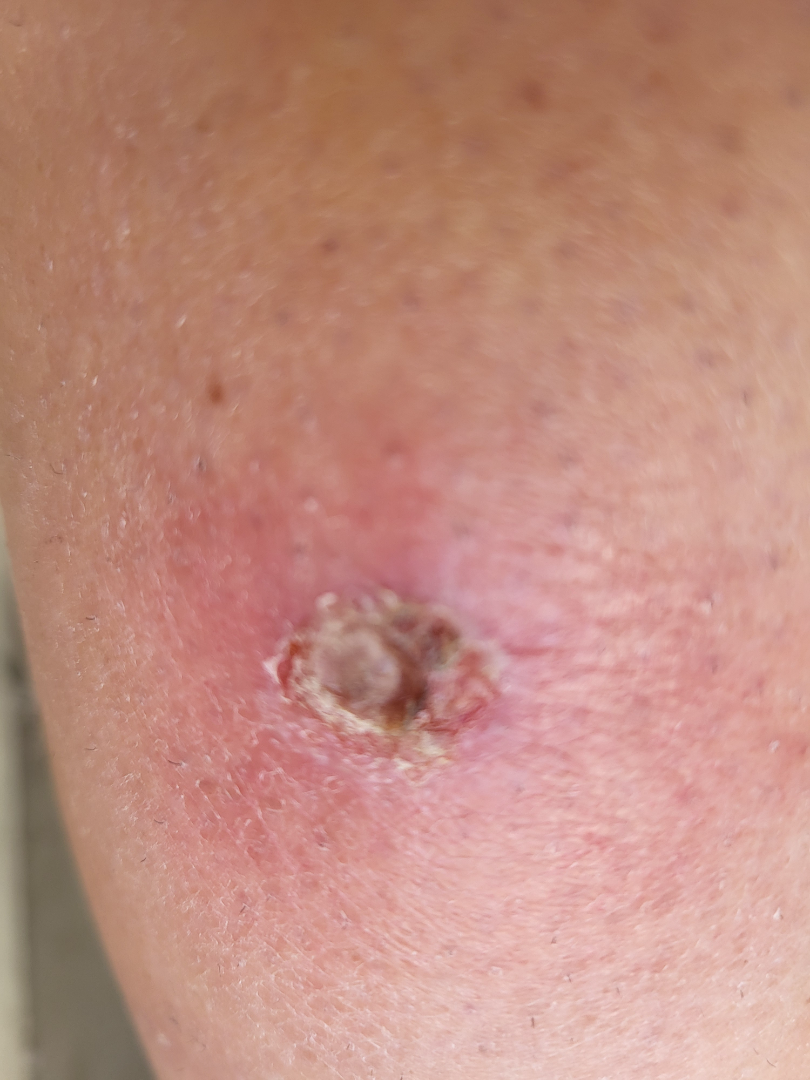A close-up photograph. The patient indicates the condition has been present for one to four weeks. The patient indicates the lesion is fluid-filled. The patient is a female aged 40–49. The leg is involved. No relevant systemic symptoms. On remote dermatologist review, Impetigo and SCC/SCCIS were each considered, in no particular order.